A smartphone photograph of a skin lesion; a subject 47 years of age: 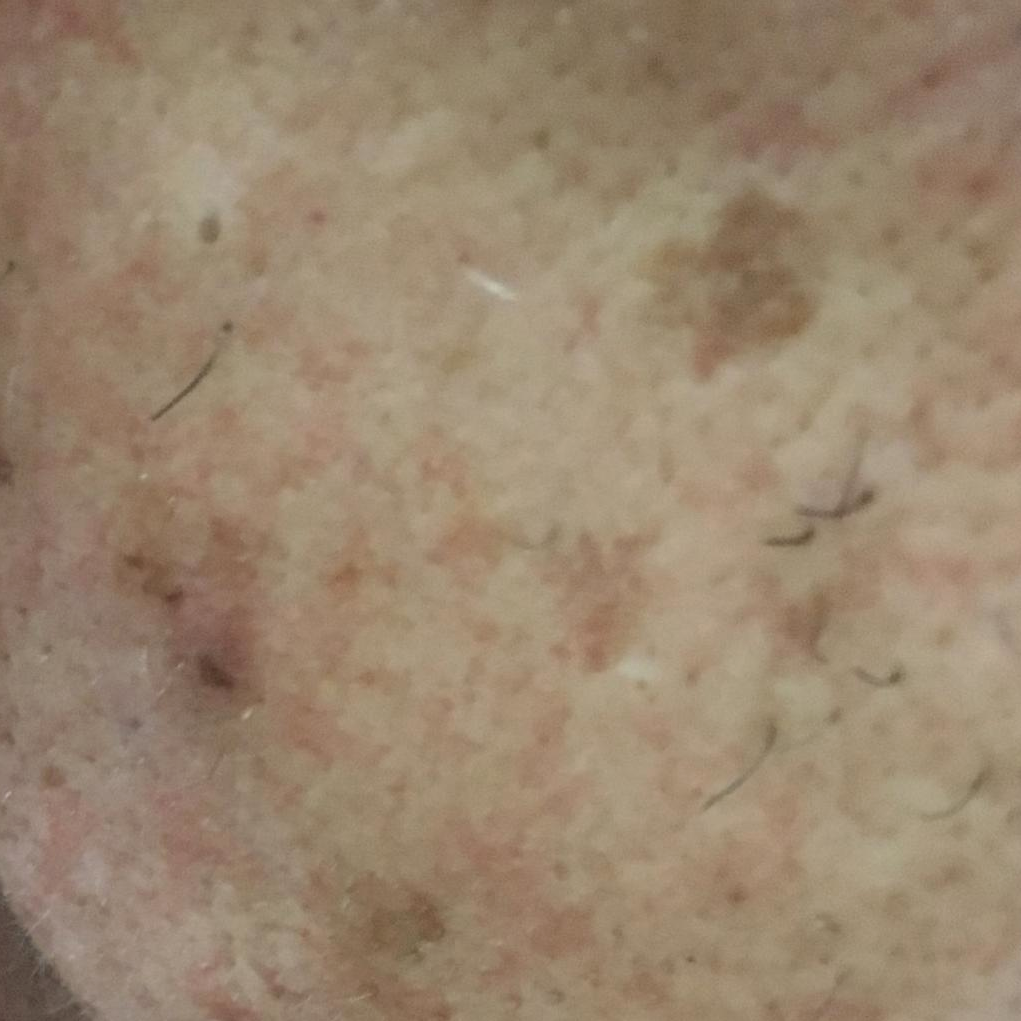The lesion is on the face.
The clinical impression was an actinic keratosis.